A dermoscopy image of a single skin lesion.
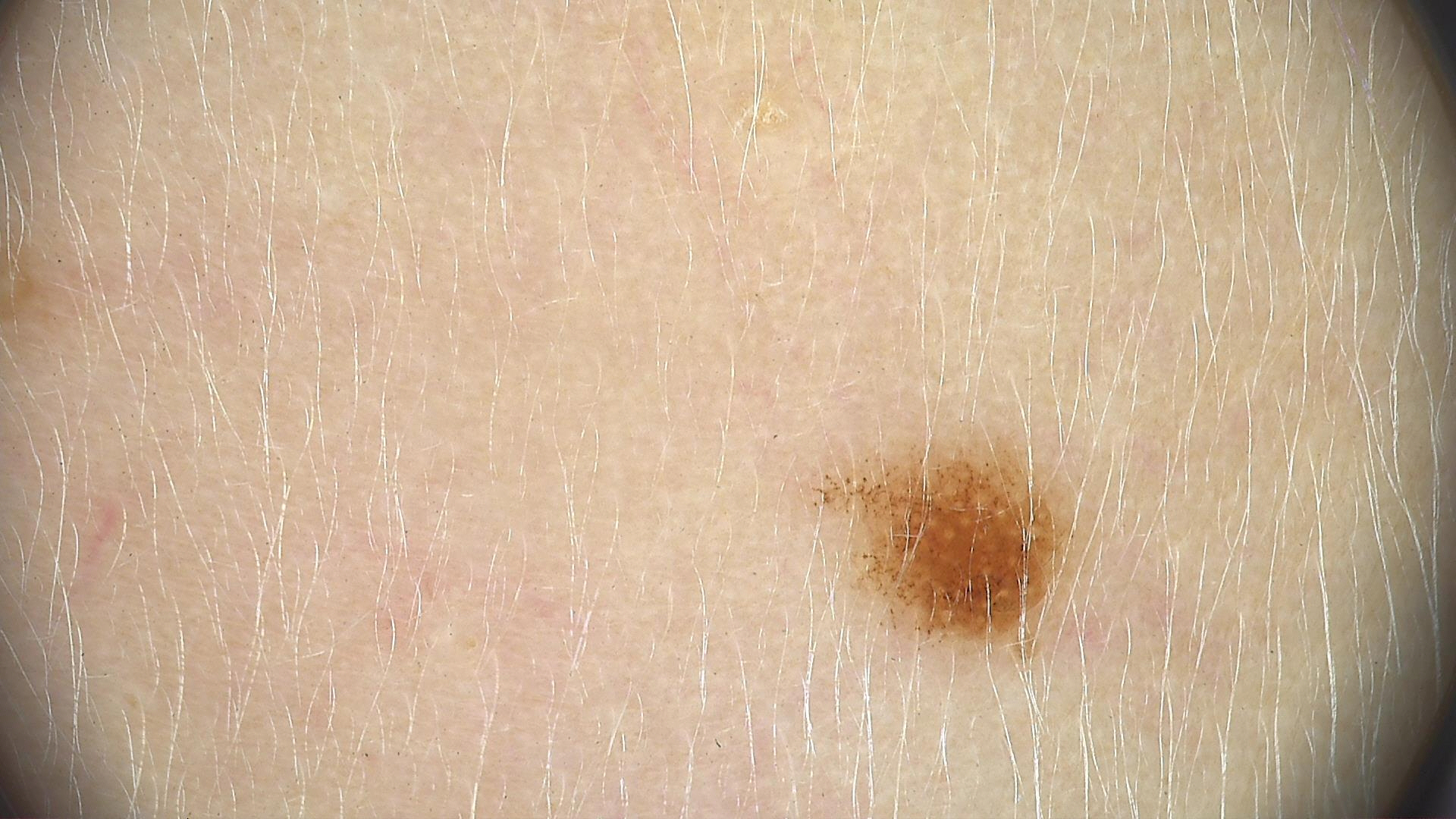Impression: Labeled as a dysplastic junctional nevus.